A clinical photograph showing a skin lesion · a male patient age 51.
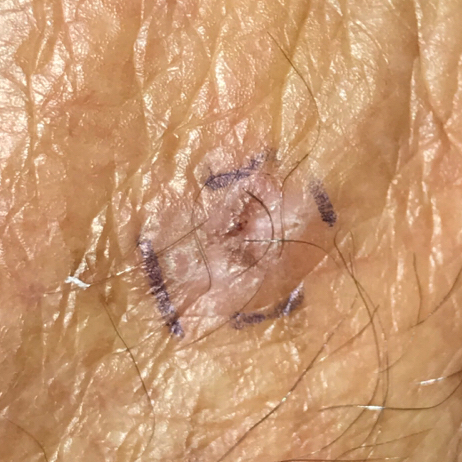Histopathologically confirmed as an actinic keratosis.